Reported lesion symptoms include itching · self-categorized by the patient as a rash · the lesion involves the back of the hand · this image was taken at an angle · reported duration is about one day · the contributor is a male aged 40–49 · the lesion is described as flat and raised or bumpy:
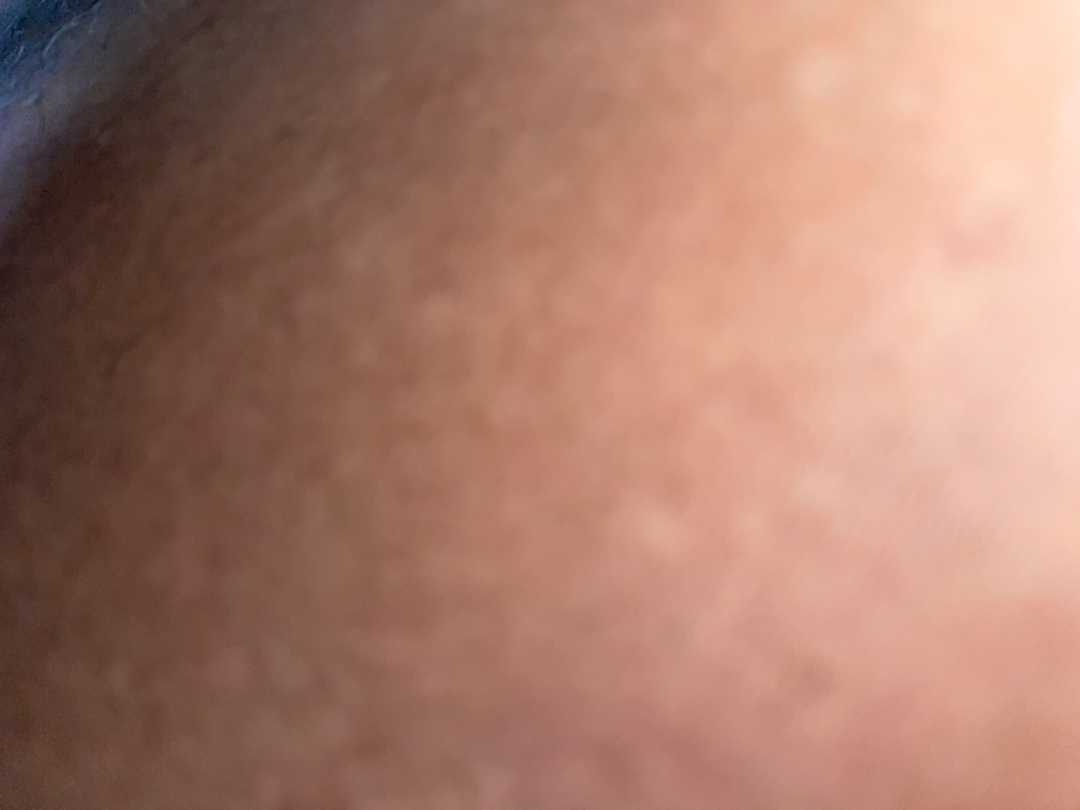The skin condition could not be confidently assessed from this image.